A dermatoscopic image of a skin lesion:
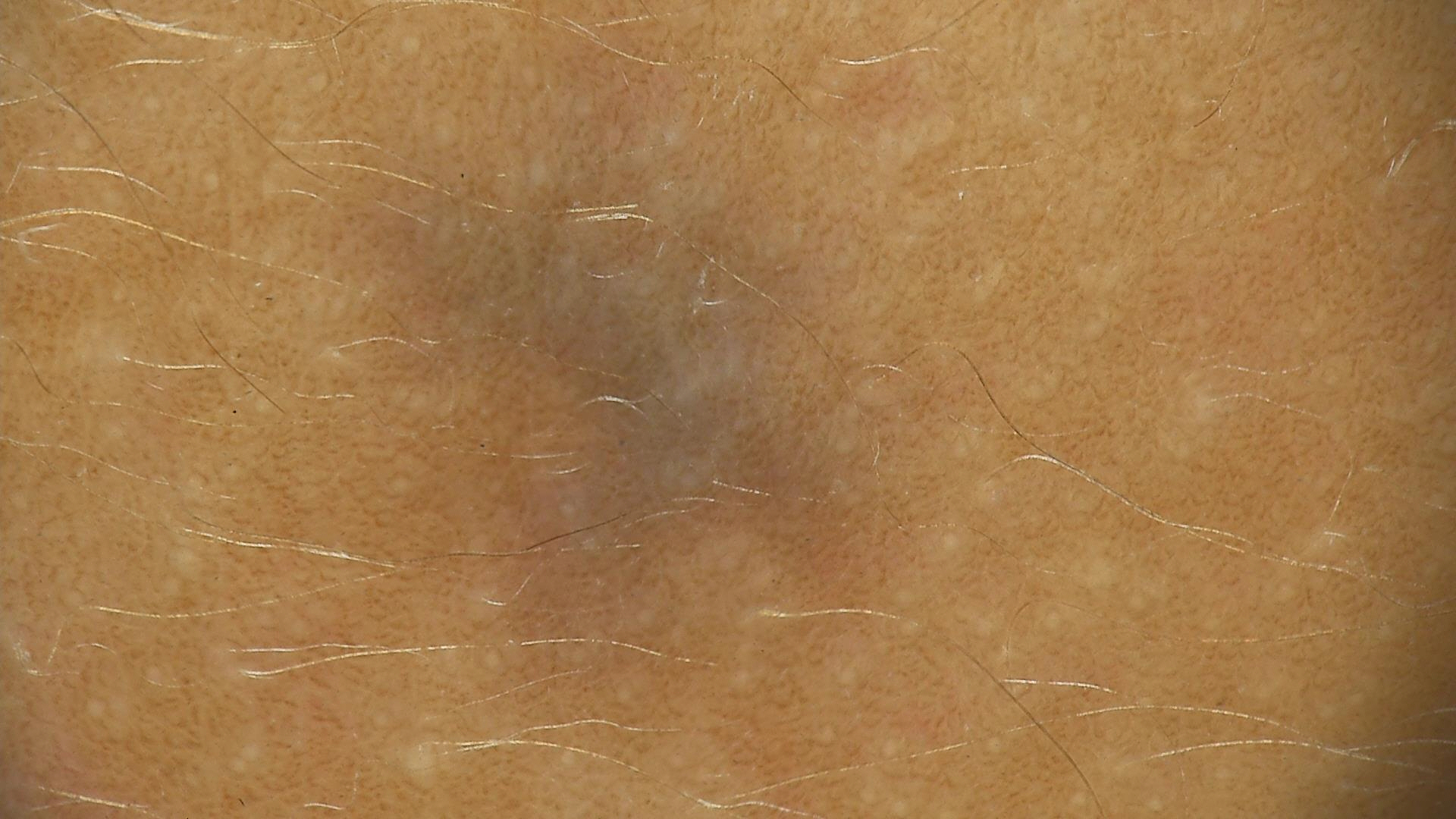Findings: This is a banal, dermal lesion. Conclusion: Consistent with a blue nevus.